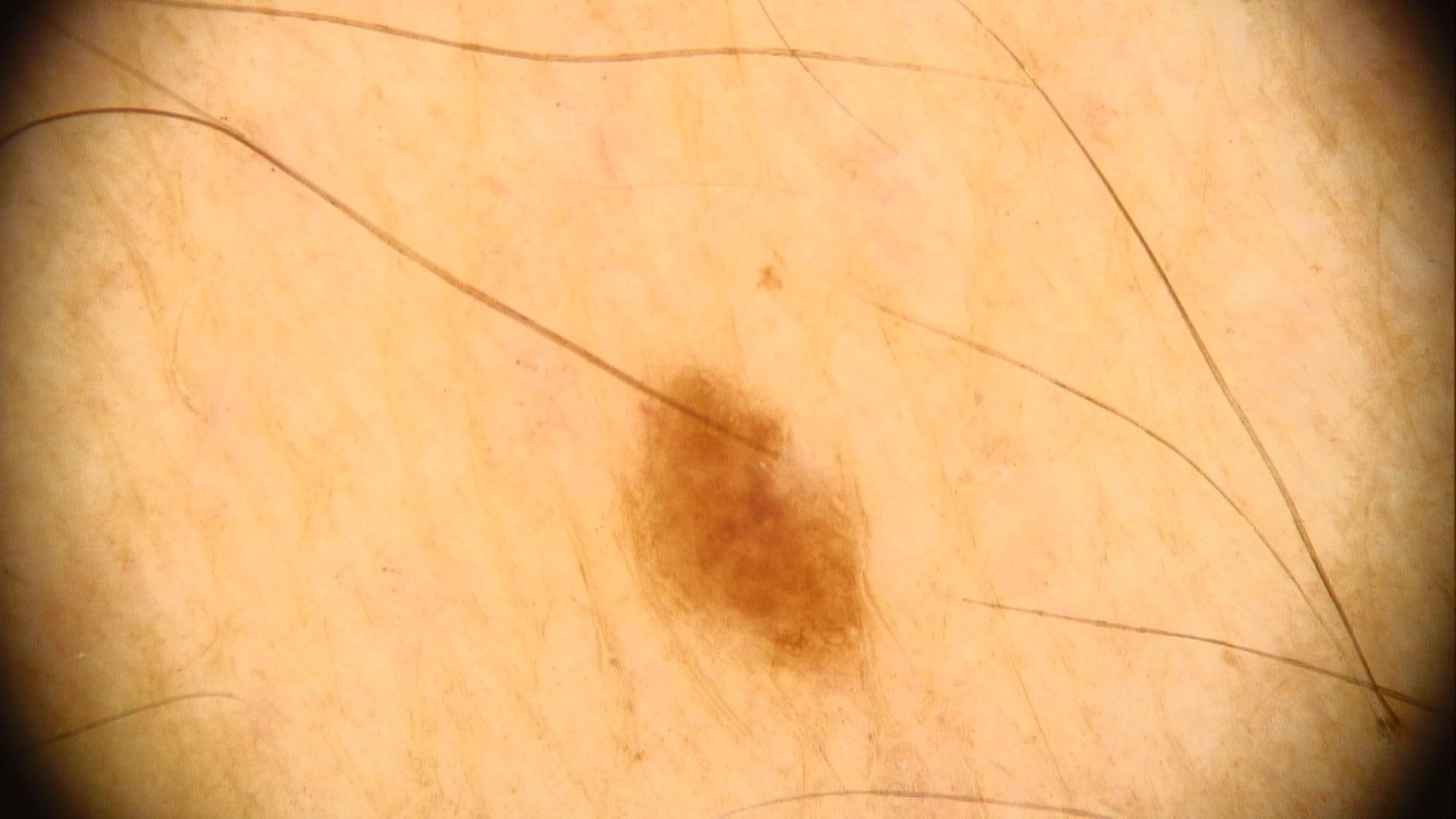A male subject aged 38 to 42. The lesion was found on a lower extremity. Clinically diagnosed as a nevus.